A dermoscopic close-up of a skin lesion.
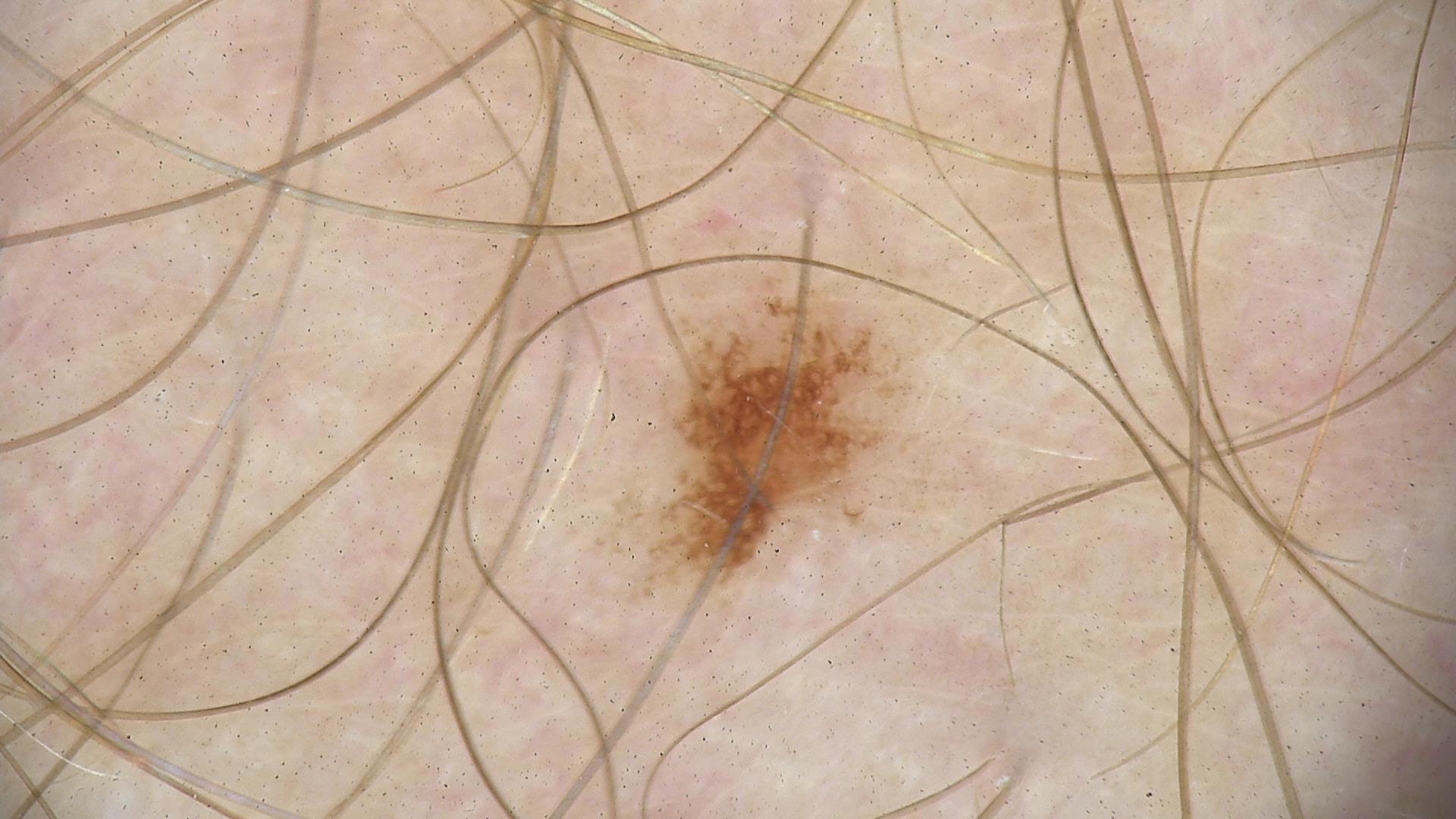label = dysplastic junctional nevus (expert consensus).